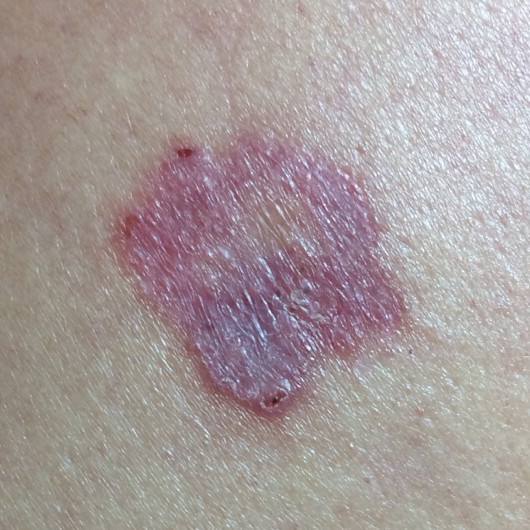Q: Patient demographics?
A: male, in their early 50s
Q: What does the exposure history note?
A: prior skin cancer (patient or family)
Q: What kind of image is this?
A: clinical photograph
Q: What is the patient's skin type?
A: II
Q: What is the anatomic site?
A: the back
Q: How large is the lesion?
A: approx. 23 × 21 mm
Q: What does the patient describe?
A: pain, growth, bleeding, itching, elevation
Q: What is the diagnosis?
A: basal cell carcinoma (biopsy-proven)